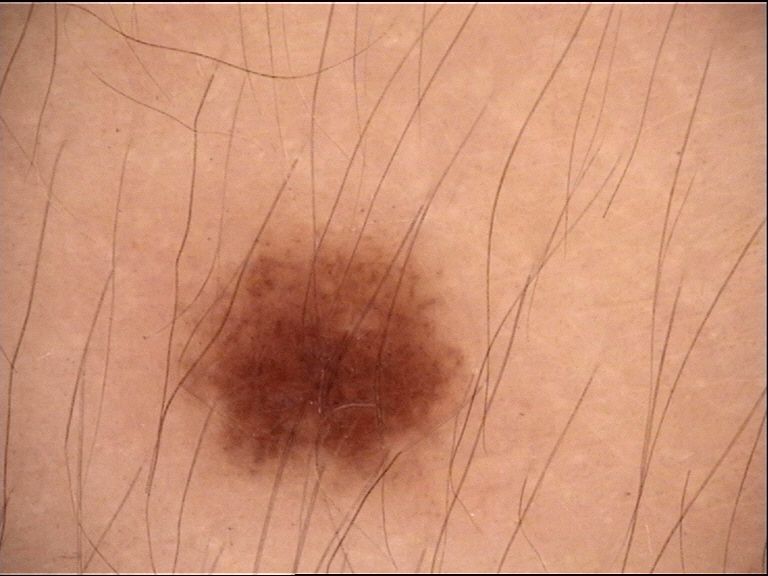{"diagnosis": {"name": "junctional nevus", "code": "jb", "malignancy": "benign", "super_class": "melanocytic", "confirmation": "expert consensus"}}